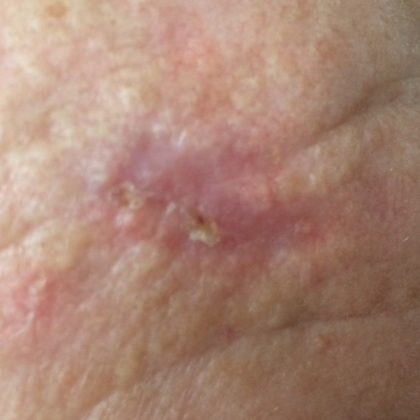modality: smartphone clinical photo; anatomic site: the face; patient-reported symptoms: growth, itching, bleeding / no change in appearance; diagnosis: basal cell carcinoma (biopsy-proven).